This is a dermoscopic photograph of a skin lesion:
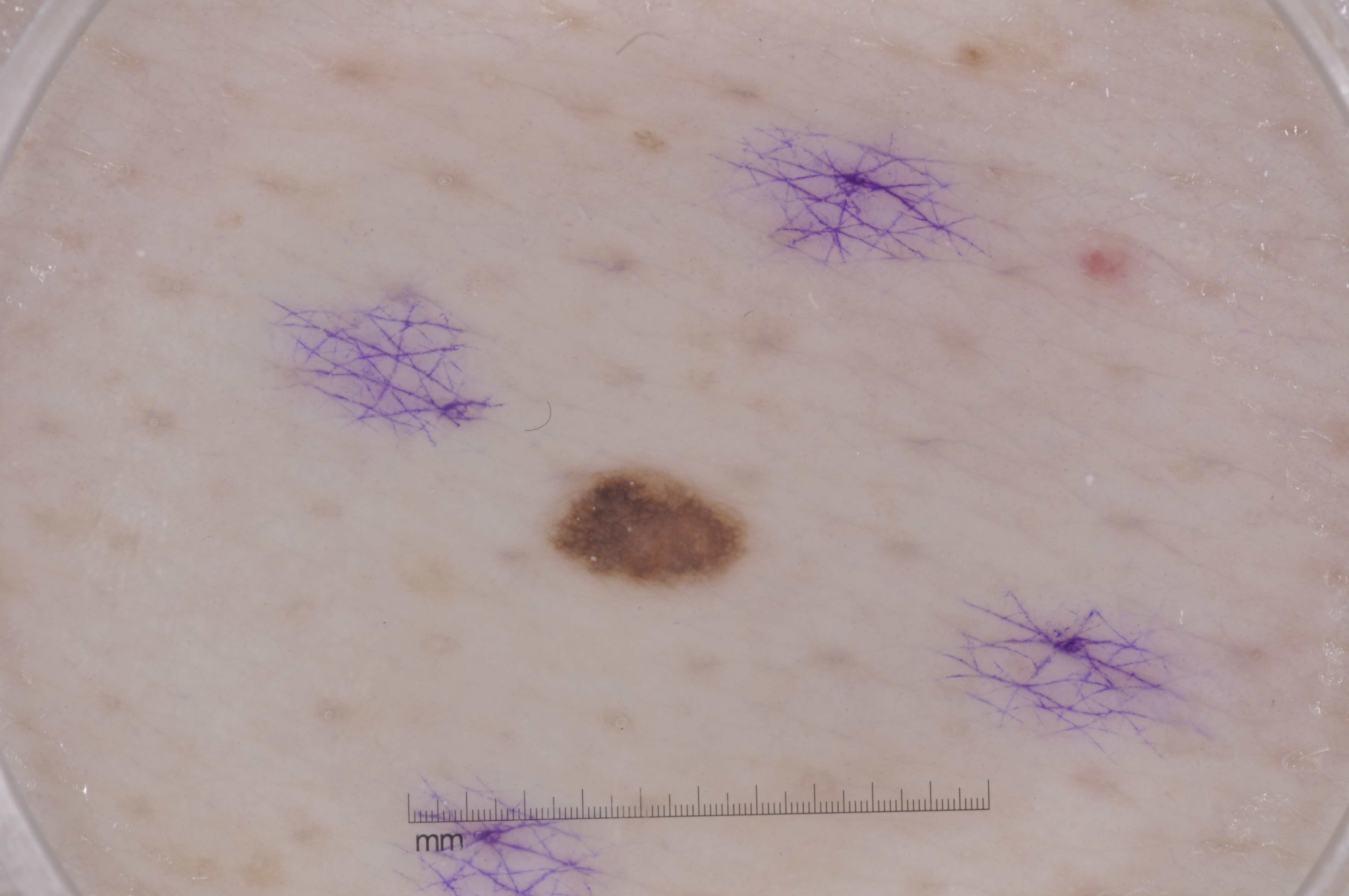In (x1, y1, x2, y2) order, the lesion's extent is bbox=[542, 462, 754, 594].
The lesion covers approximately 2% of the dermoscopic field.
Dermoscopically, the lesion shows pigment network and milia-like cysts, with no negative network or streaks.
Expert review diagnosed this as a melanocytic nevus, a benign lesion.